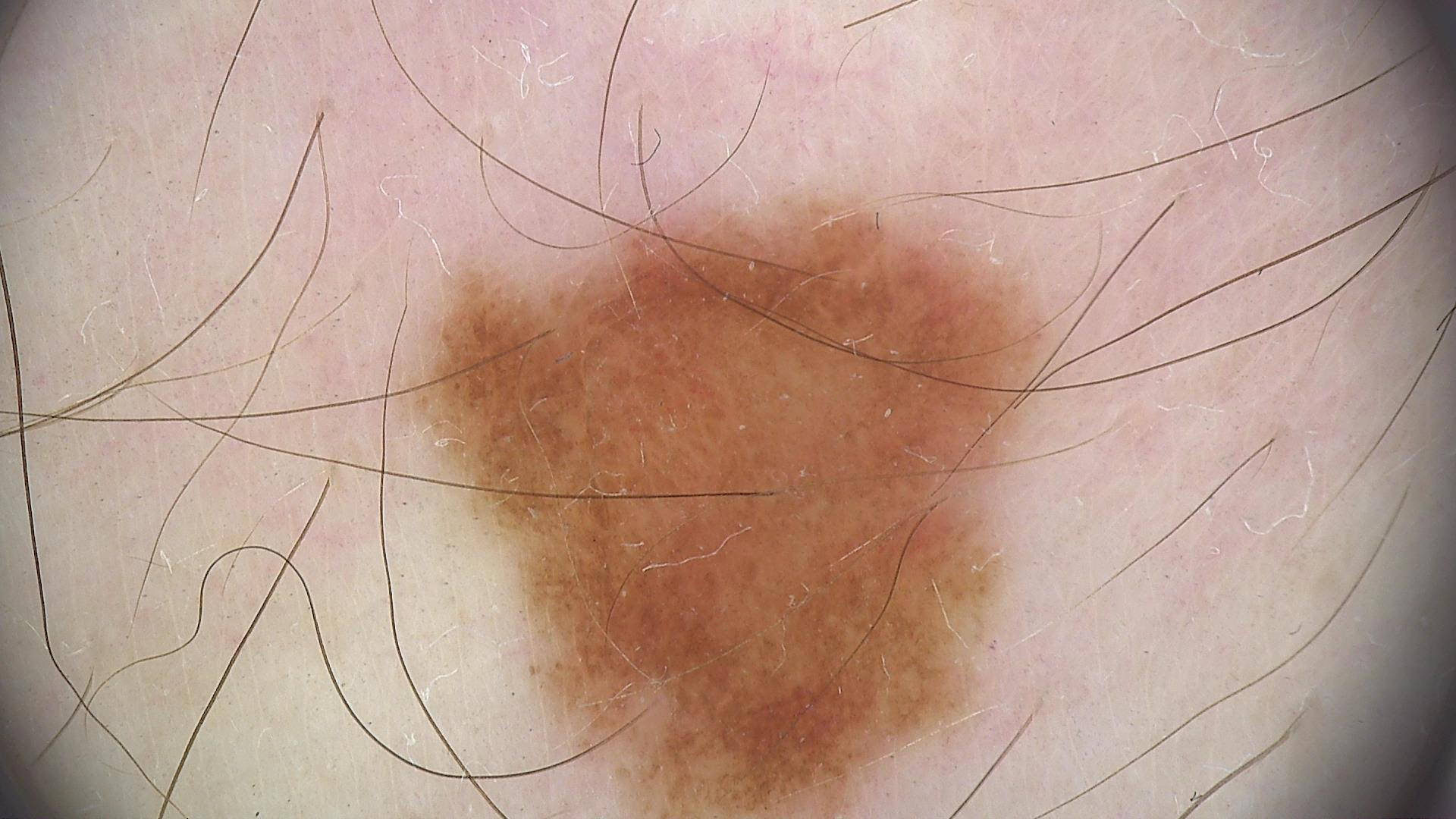imaging=dermoscopy | class=dysplastic junctional nevus (expert consensus).